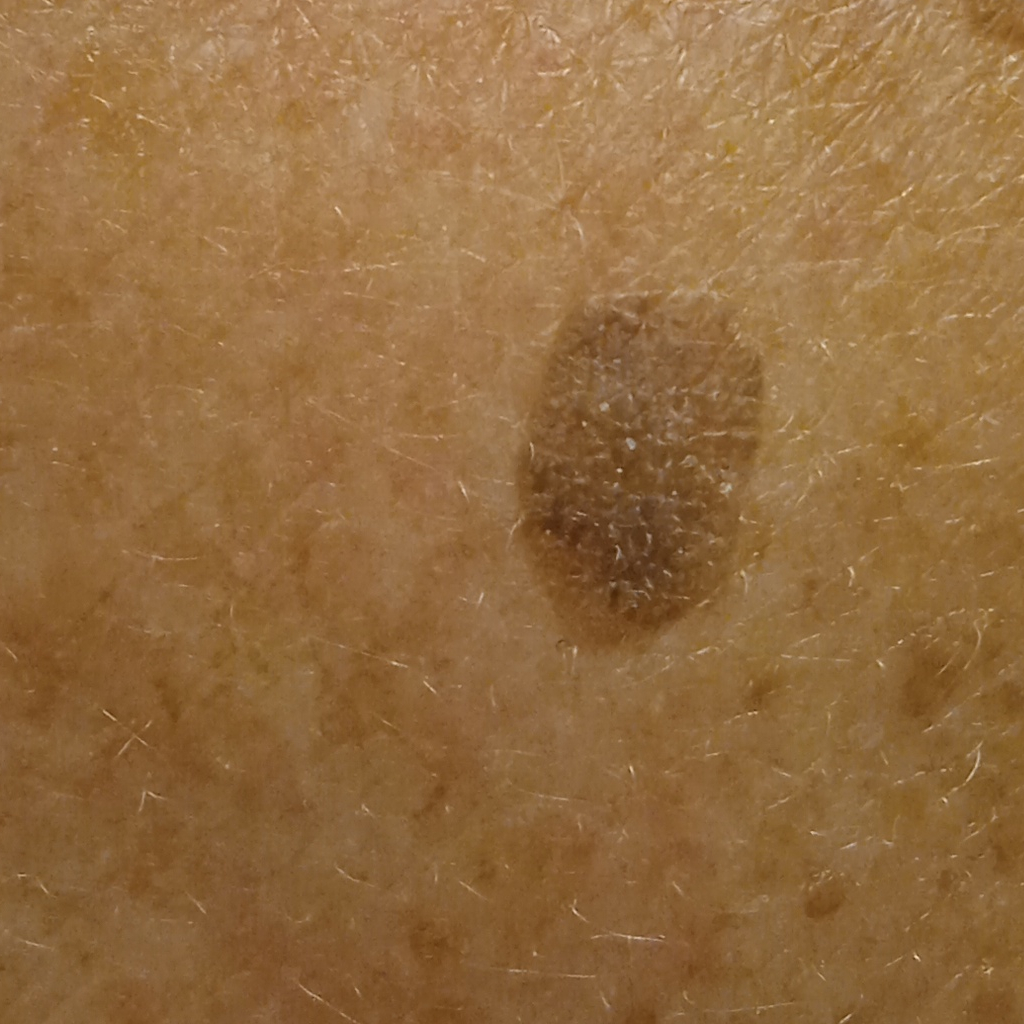nevus count — numerous melanocytic nevi; patient — female, 78 years old; referral context — research study (no referral diagnosis); modality — clinical photograph; sun reaction — skin tans without first burning; location — the back; size — 9.6 mm; assessment — seborrheic keratosis (dermatologist consensus).